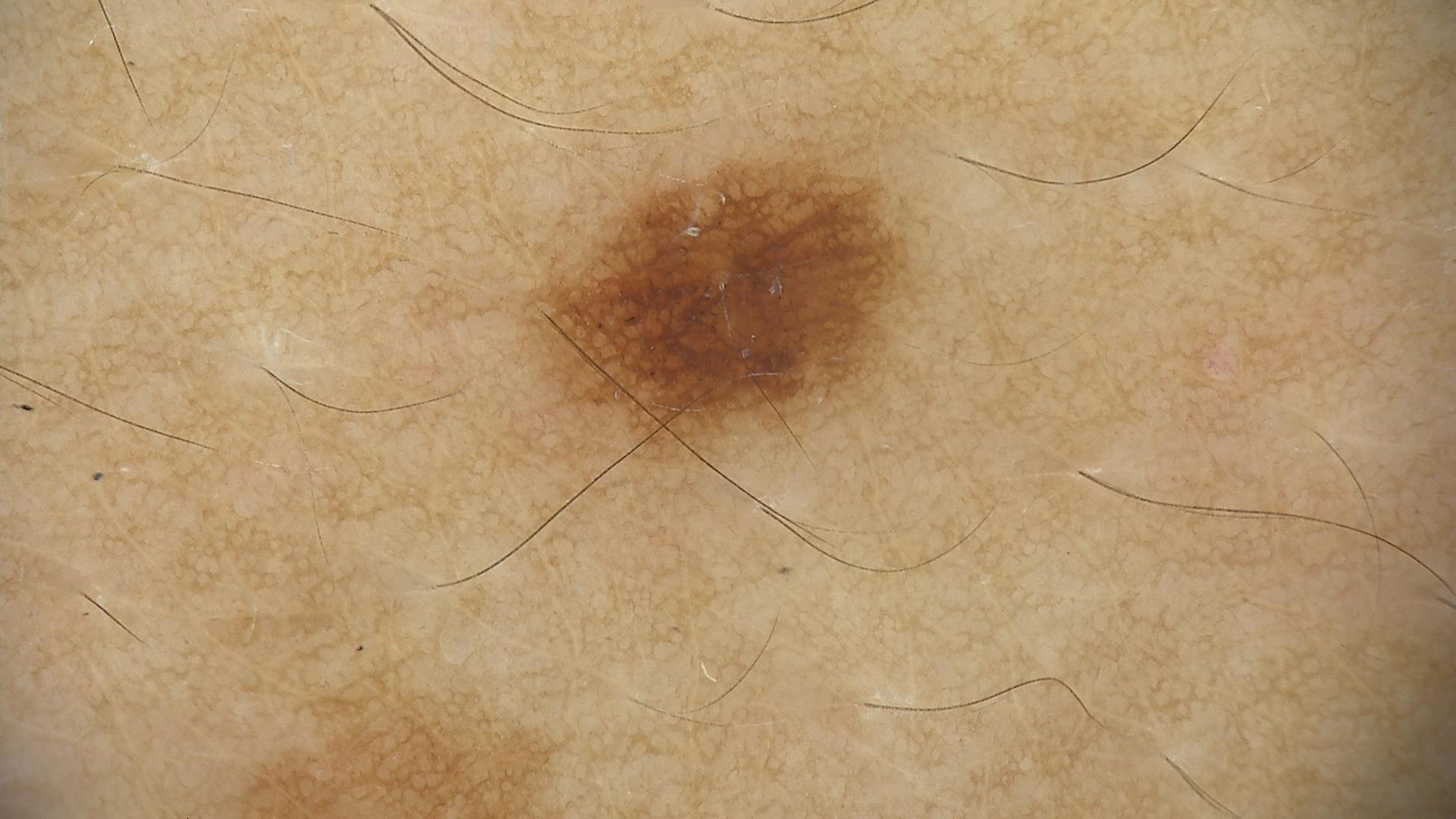Case:
• class — dysplastic junctional nevus (expert consensus)